A dermoscopic image of a skin lesion.
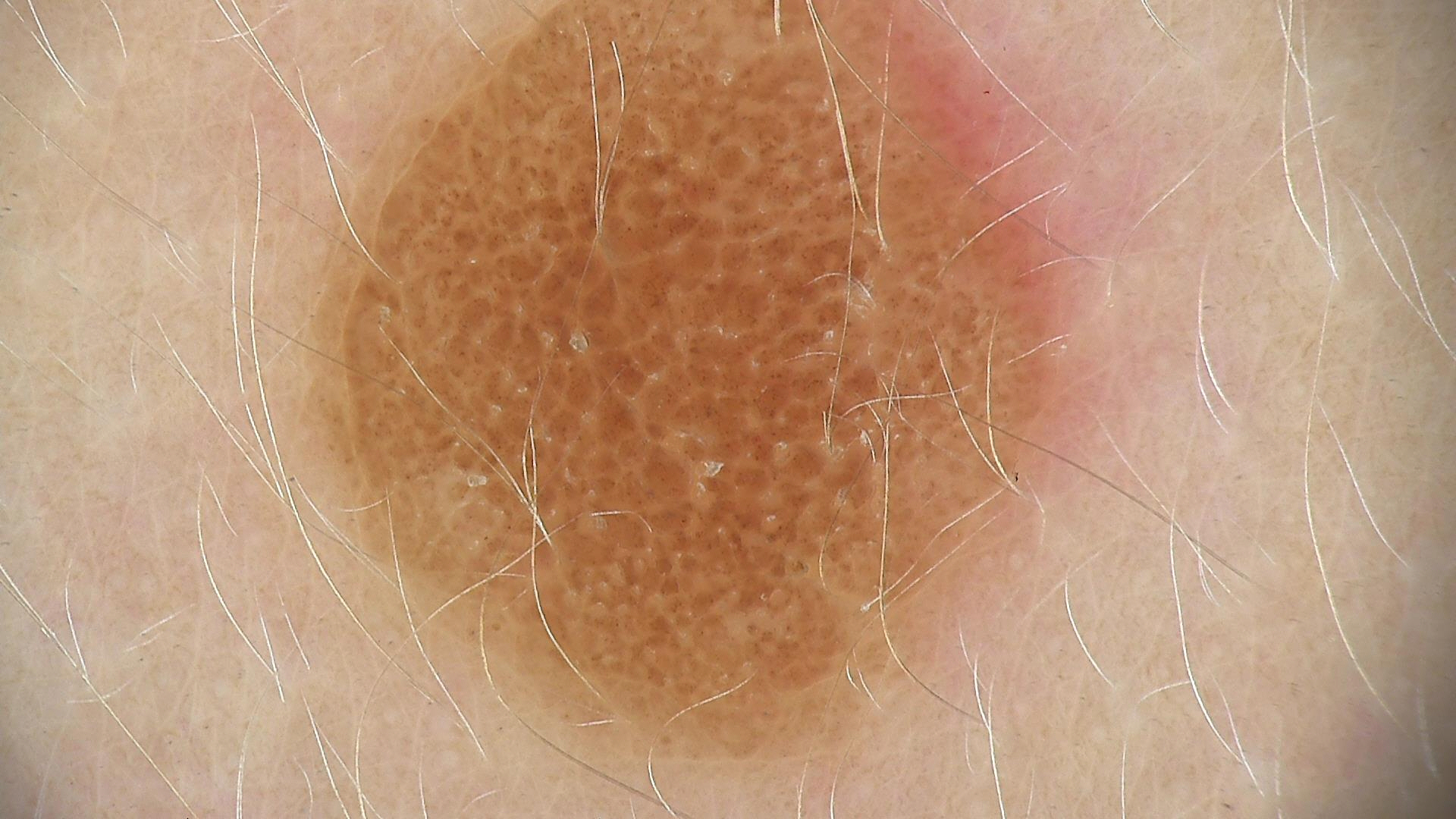This is a banal lesion.
Classified as a compound nevus.